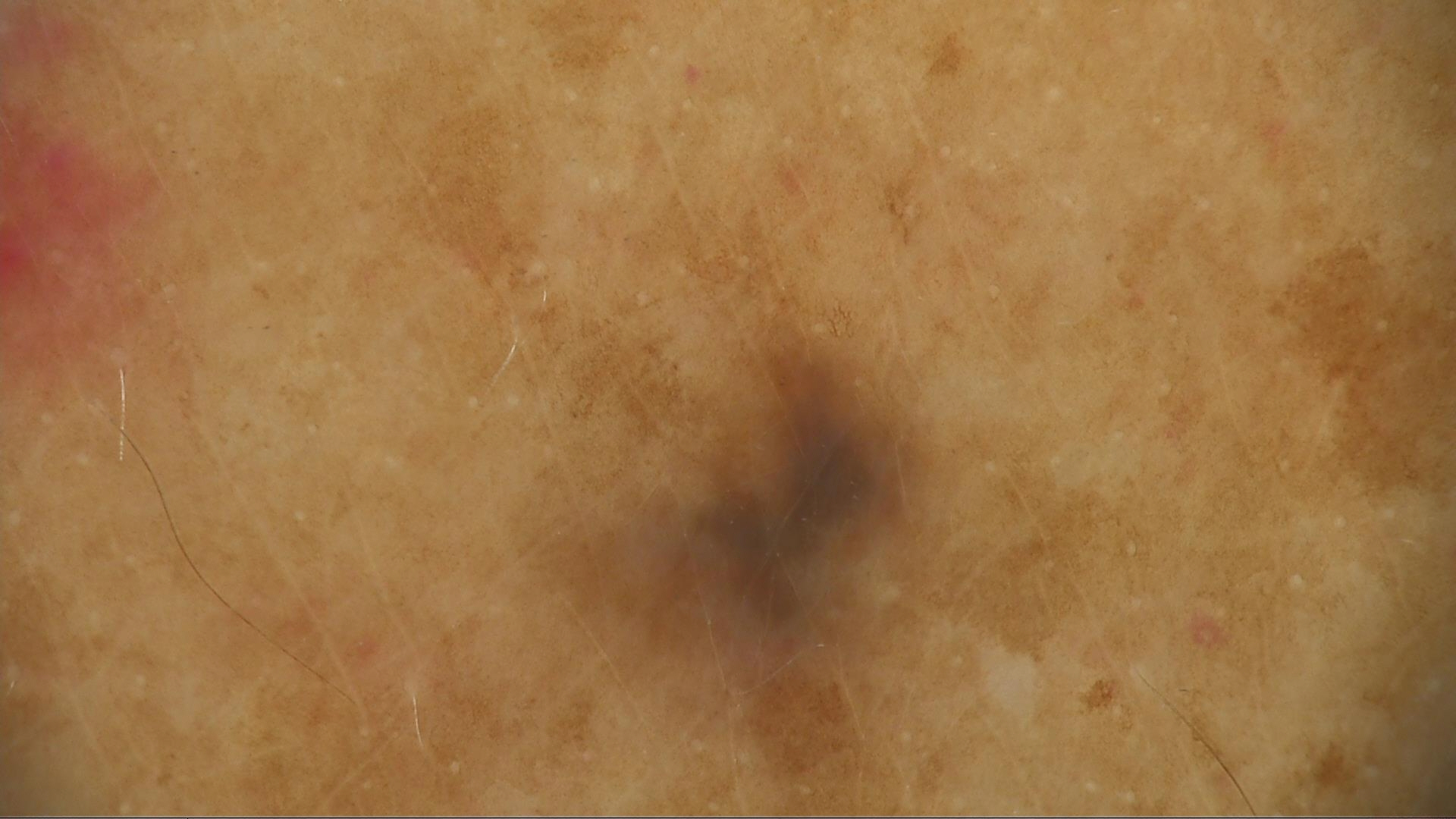{"image": "dermoscopy", "diagnosis": {"name": "blue nevus", "code": "bdb", "malignancy": "benign", "super_class": "melanocytic", "confirmation": "expert consensus"}}